A skin lesion imaged with a dermatoscope:
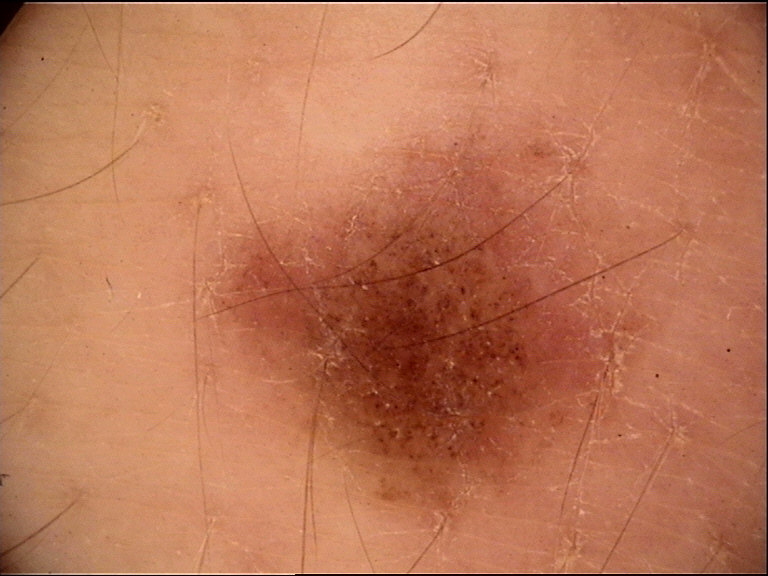Labeled as a dysplastic junctional nevus.